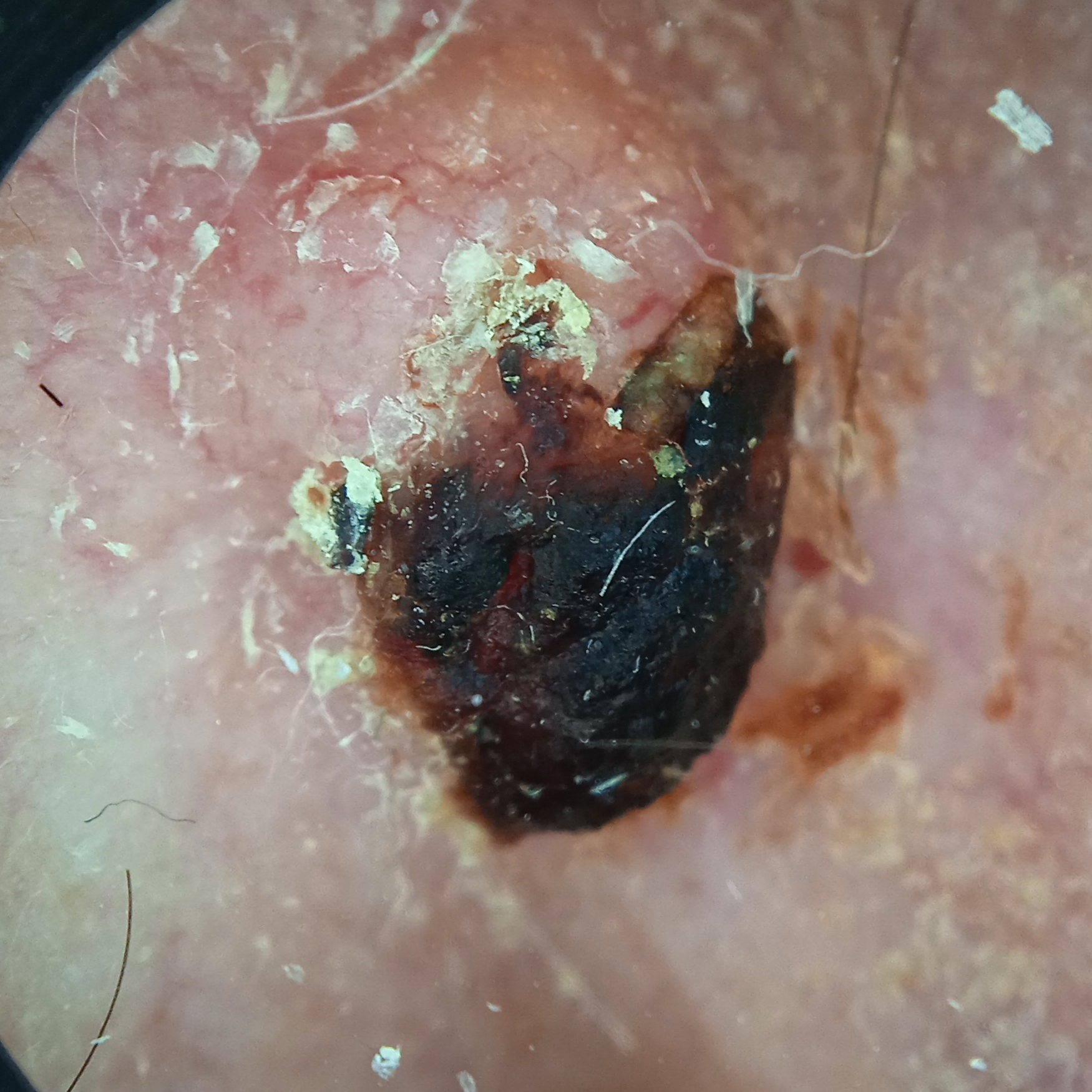referral — clinical suspicion of basal cell carcinoma | image — dermoscopy | relevant history — no immunosuppression | subject — male, age 83 | diameter — 8 mm | diagnosis — basal cell carcinoma (biopsy-proven).